Self-categorized by the patient as a rash · the lesion is described as fluid-filled, raised or bumpy and rough or flaky · reported duration is more than one year · the back of the hand and palm are involved · the patient reports itching, bothersome appearance and pain · the photo was captured at an angle:
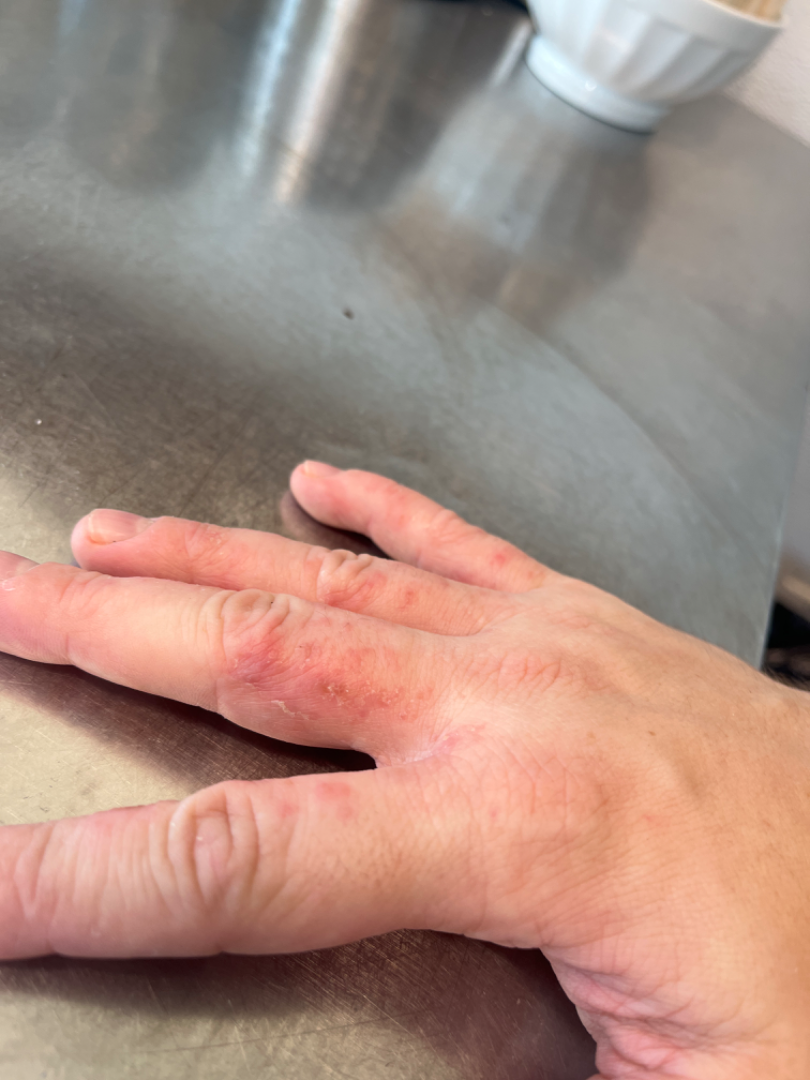| field | value |
|---|---|
| impression | Eczema (favored); Irritant Contact Dermatitis (considered); Scabies (considered) |